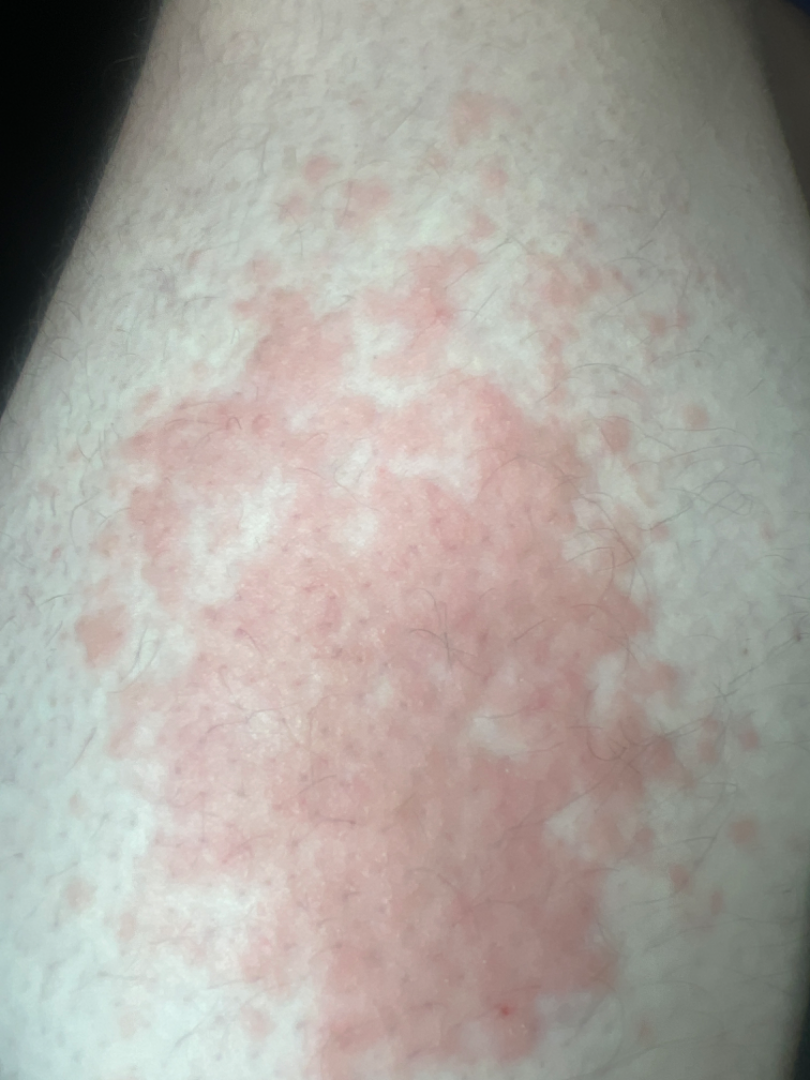{
  "body_site": "leg",
  "shot_type": "close-up",
  "differential": {
    "leading": [
      "Acute dermatitis, NOS"
    ]
  }
}